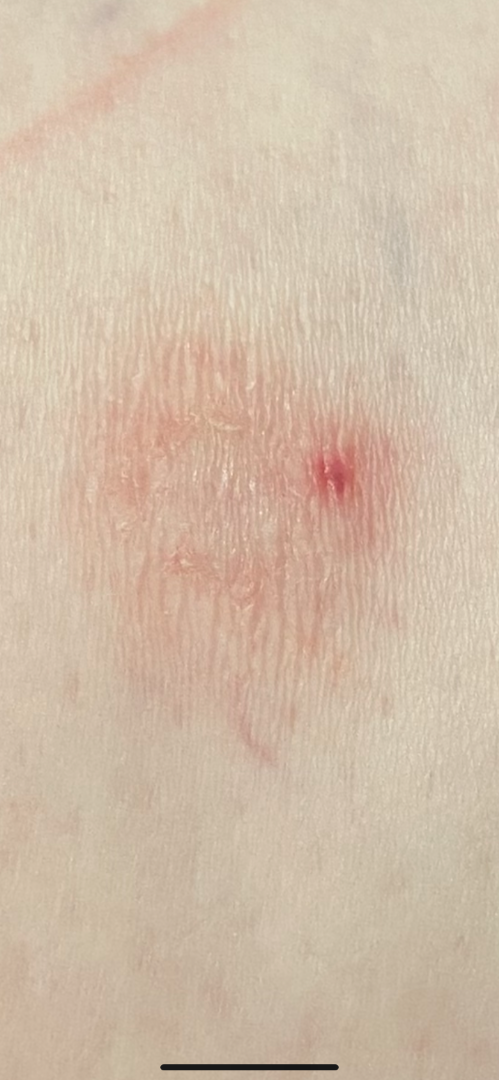The skin condition could not be confidently assessed from this image. The lesion involves the leg. Close-up view. No relevant lesion symptoms reported. The patient also reports fatigue. The patient reports the condition has been present for one to three months. The patient described the issue as skin that appeared healthy to them.